Associated systemic symptoms include joint pain · reported duration is one to four weeks · located on the back of the hand and arm · the subject is 18–29, female · the lesion is associated with darkening · texture is reported as flat · the photo was captured at an angle: 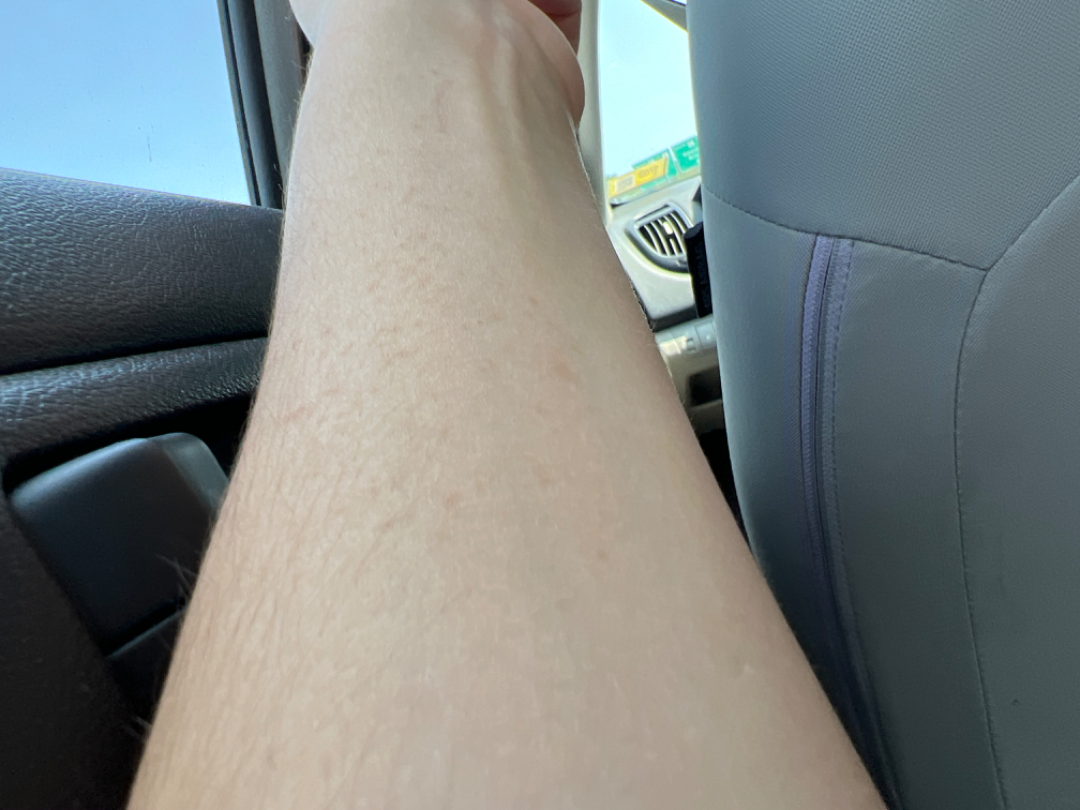The reviewing dermatologist's impression was: Viral Exanthem, Hypersensitivity and Allergic Contact Dermatitis were considered with similar weight.